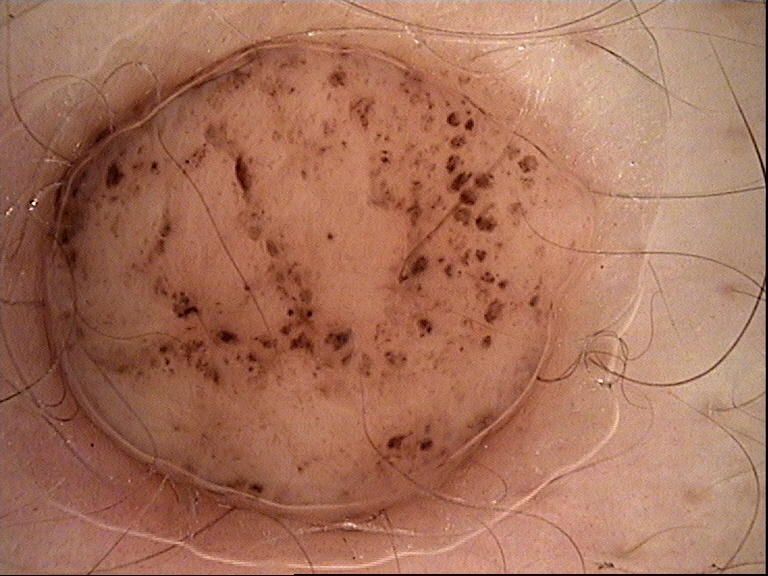Case:
– lesion type — banal
– diagnosis — dermal nevus (expert consensus)